A smartphone photograph of a skin lesion: 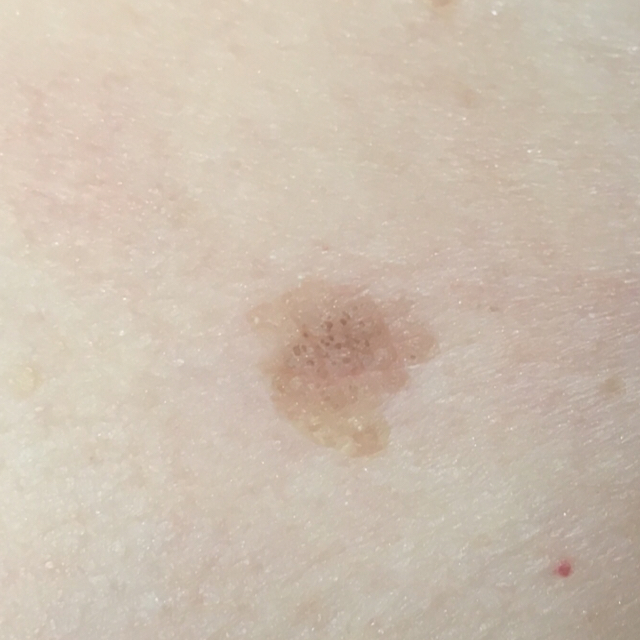region=the chest
impression=seborrheic keratosis (clinical consensus)